Self-categorized by the patient as a rash · symptoms reported: burning, pain and bothersome appearance · texture is reported as flat, fluid-filled and raised or bumpy · the front of the torso is involved · the photograph was taken at an angle · the patient is male.
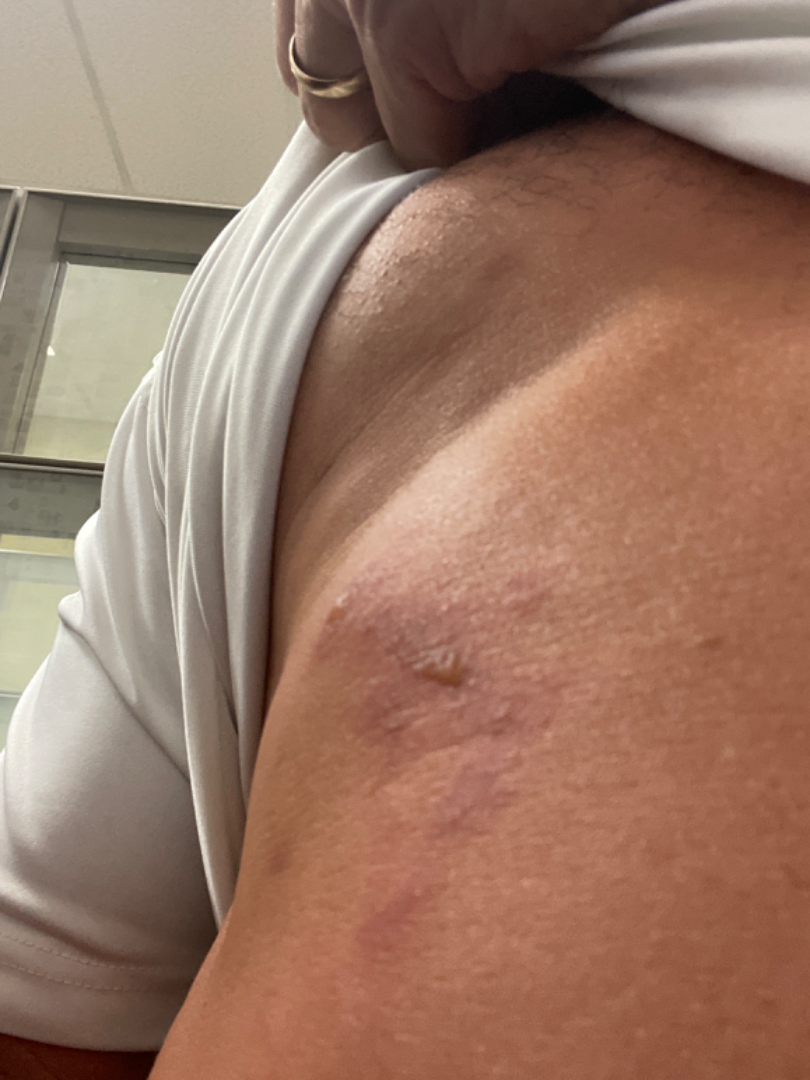dermatologist impression = one reviewing dermatologist: the leading consideration is Allergic Contact Dermatitis; the differential also includes Burn of skin